Dermoscopy of a skin lesion · a male patient about 70 years old · the patient is FST II — 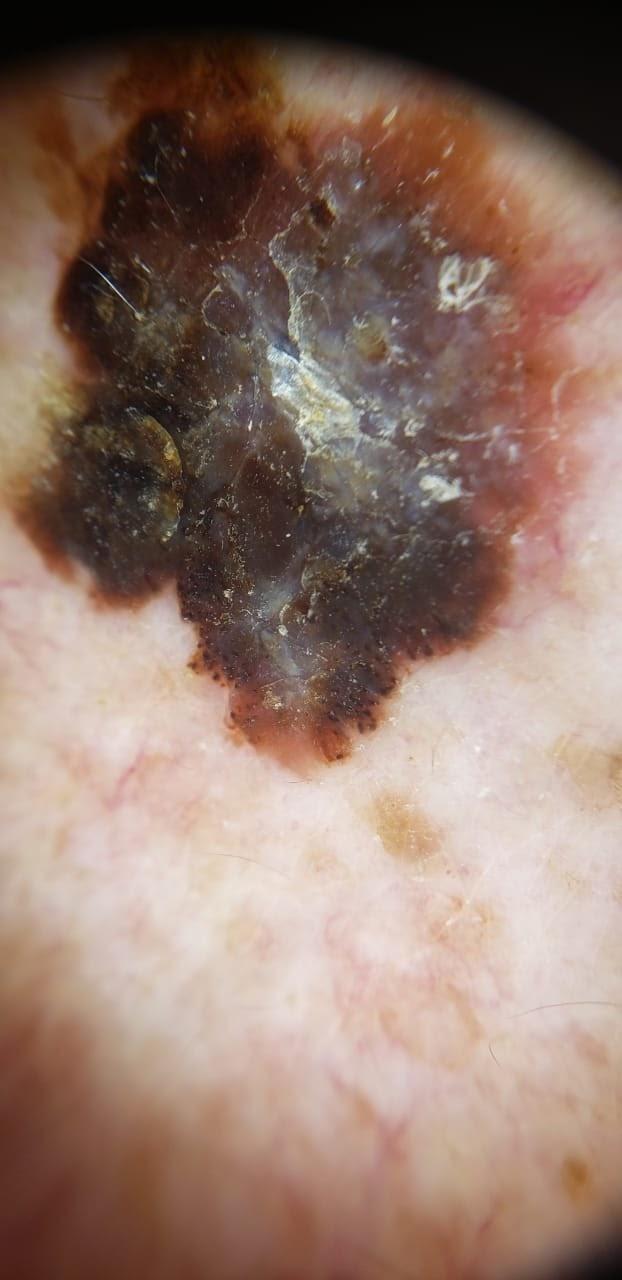Biopsy-confirmed as a skin cancer — a melanoma.